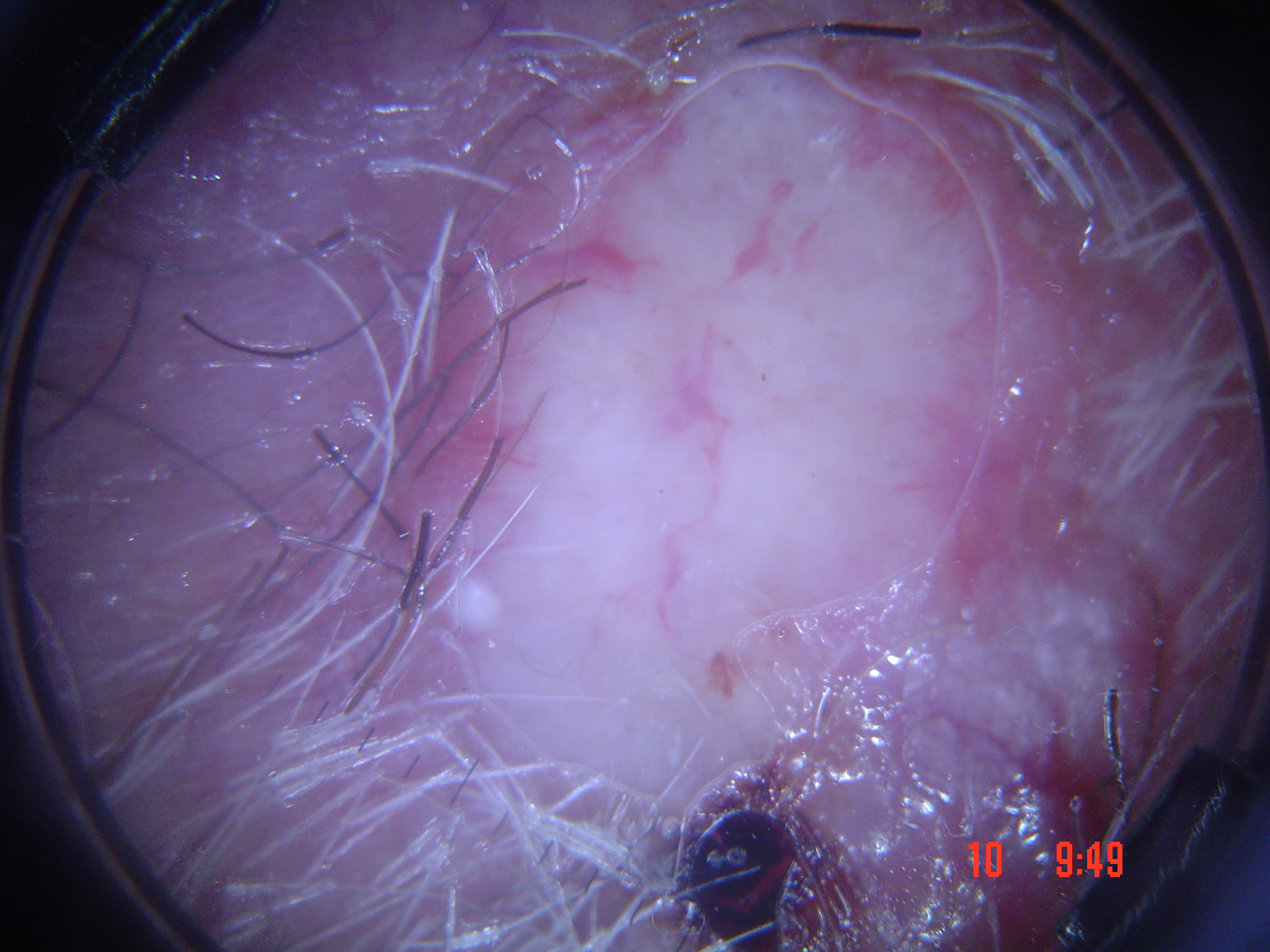label — basal cell carcinoma (biopsy-proven).